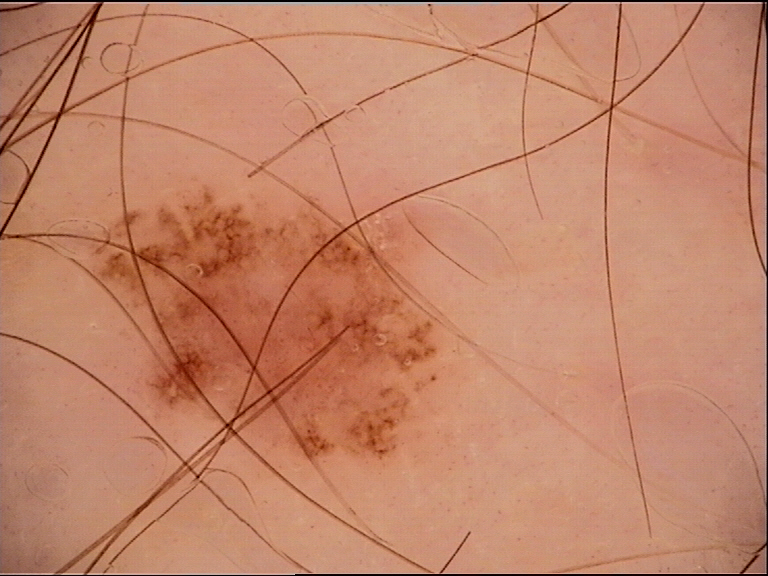Diagnosed as a dysplastic junctional nevus.